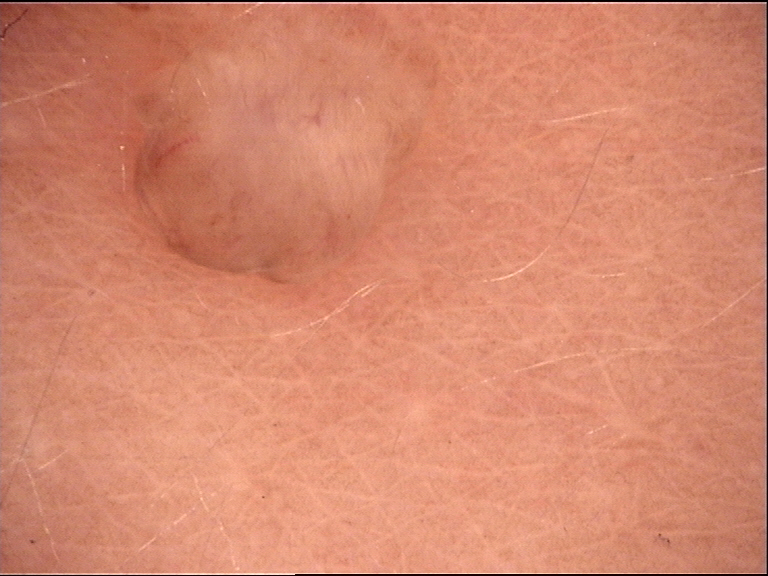image = dermatoscopy | class = dermal nevus (expert consensus).